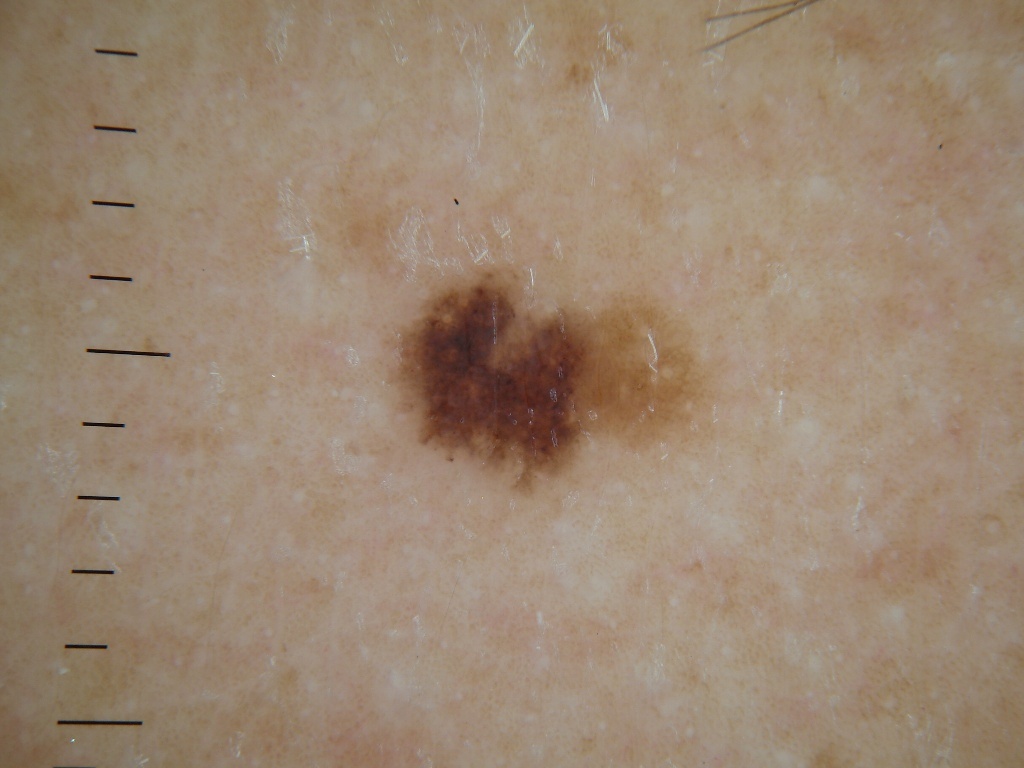Dermoscopy of a skin lesion. A female patient, aged 28-32. The lesion is located at <bbox>380, 261, 705, 496</bbox>. Dermoscopic review identifies no milia-like cysts, globules, pigment network, negative network, or streaks. Expert review diagnosed this as a melanocytic nevus.